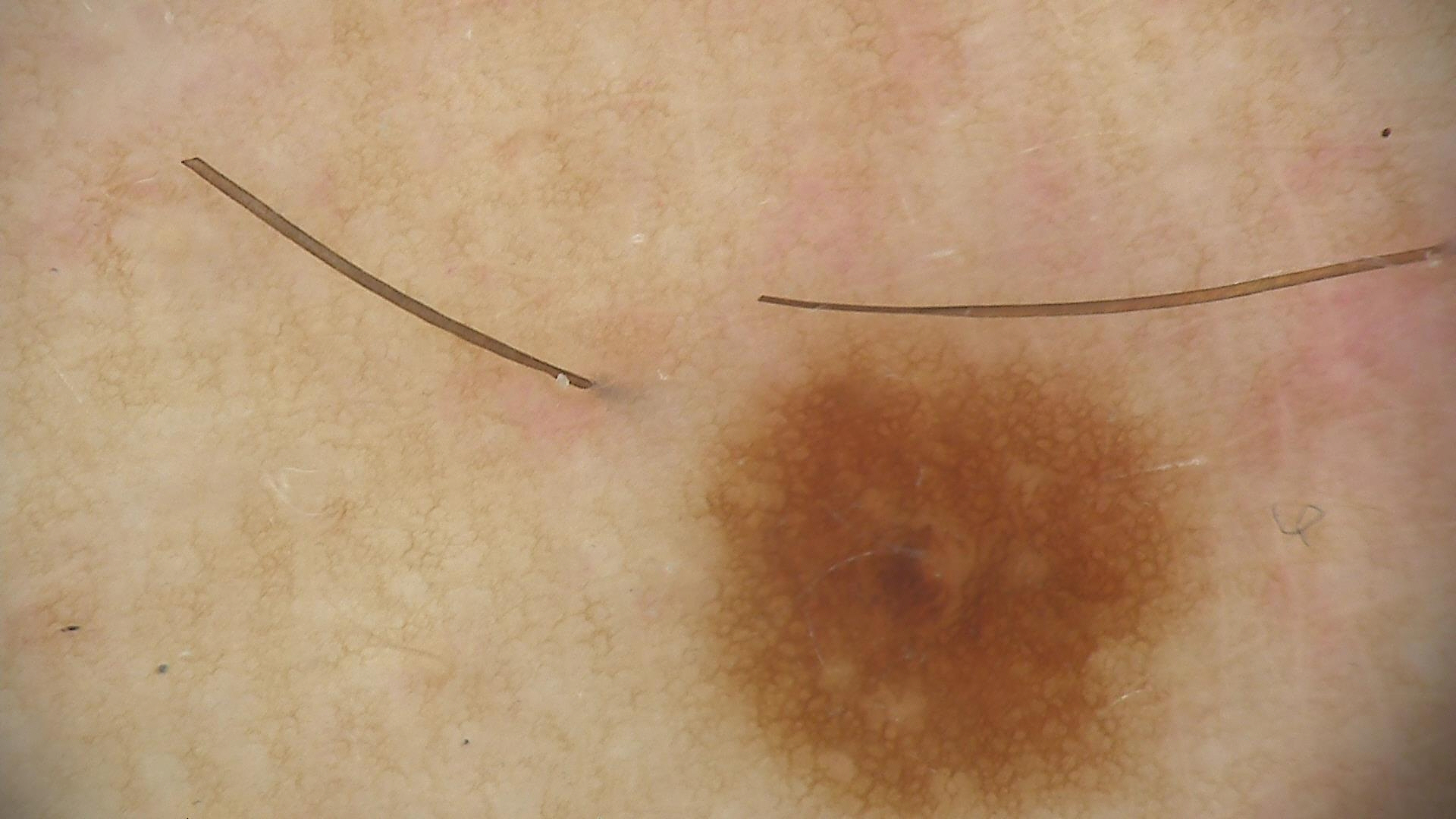Q: What was the diagnostic impression?
A: dysplastic junctional nevus (expert consensus)